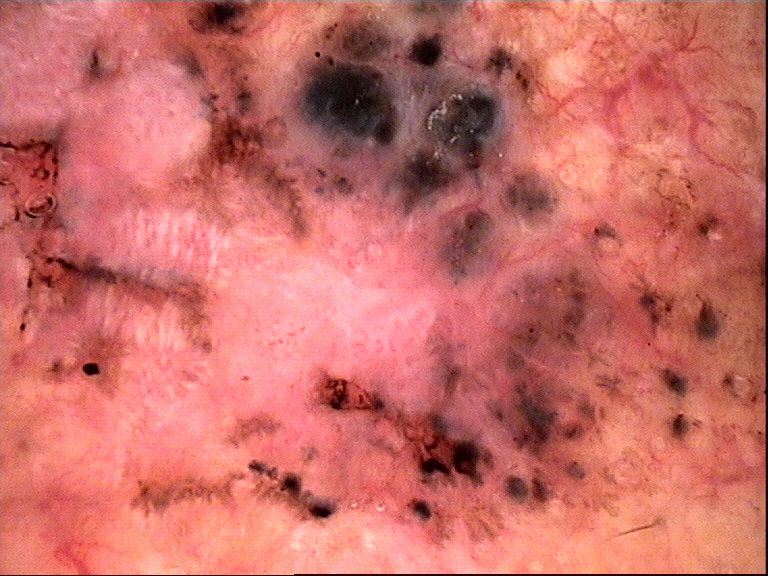The biopsy diagnosis was a keratinocytic lesion — a basal cell carcinoma.